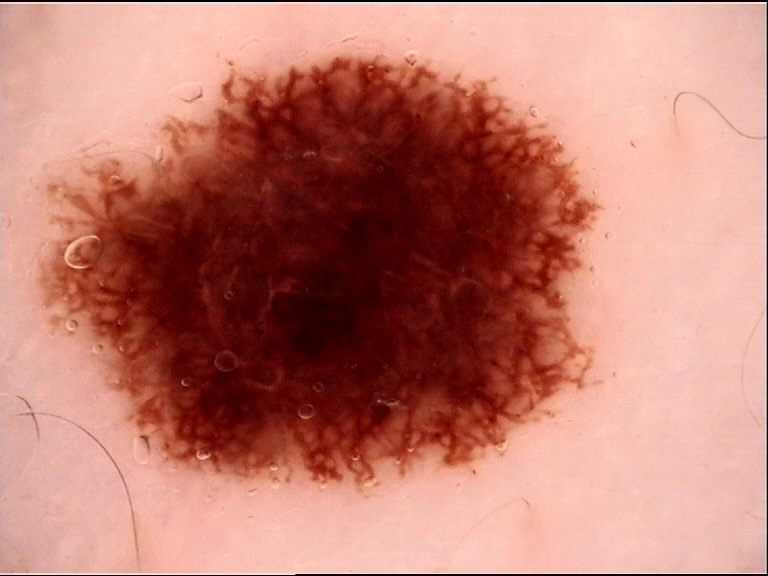Classified as a dysplastic junctional nevus.